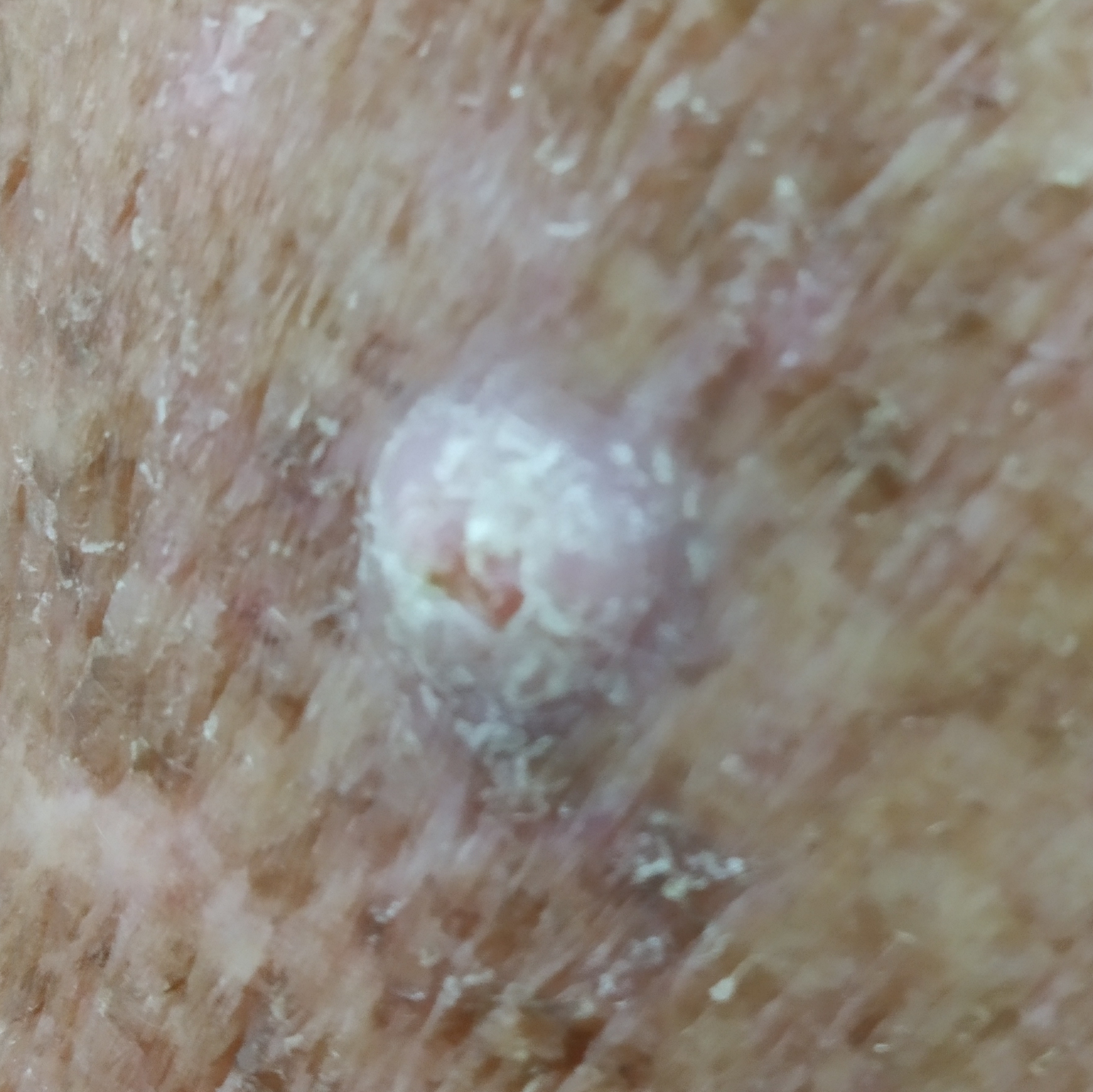{"patient": {"age": 69, "gender": "male"}, "skin_type": "III", "lesion_location": "an arm", "symptoms": {"present": ["elevation", "itching", "change in appearance", "growth"], "absent": ["bleeding", "pain"]}, "diagnosis": {"name": "squamous cell carcinoma", "code": "SCC", "malignancy": "malignant", "confirmation": "histopathology"}}